Self-categorized by the patient as acne. The lesion is associated with itching. Fitzpatrick phototype II; human graders estimated Monk skin tone scale 3–4. The lesion involves the top or side of the foot, arm and leg. Close-up view. The patient reports the lesion is raised or bumpy. The patient is a male aged 40–49. The patient reports associated fatigue. Present for one to three months.
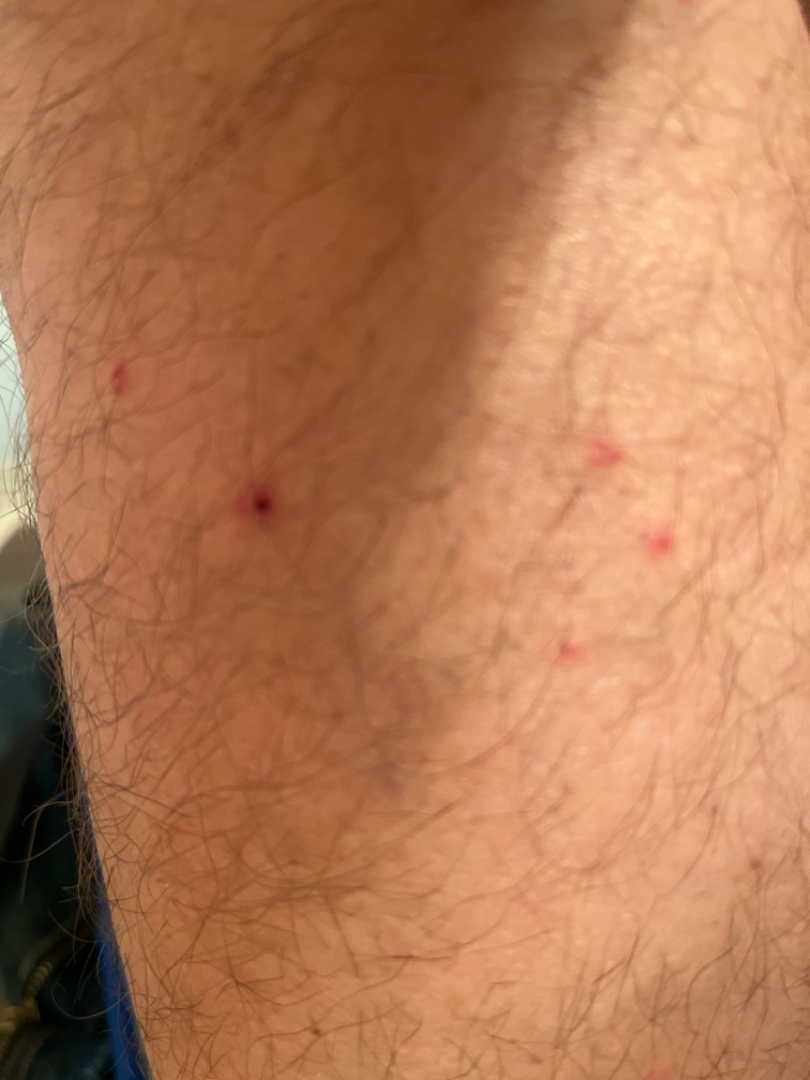Notes:
• assessment: the differential is split between Pityriasis lichenoides, Folliculitis and Insect Bite